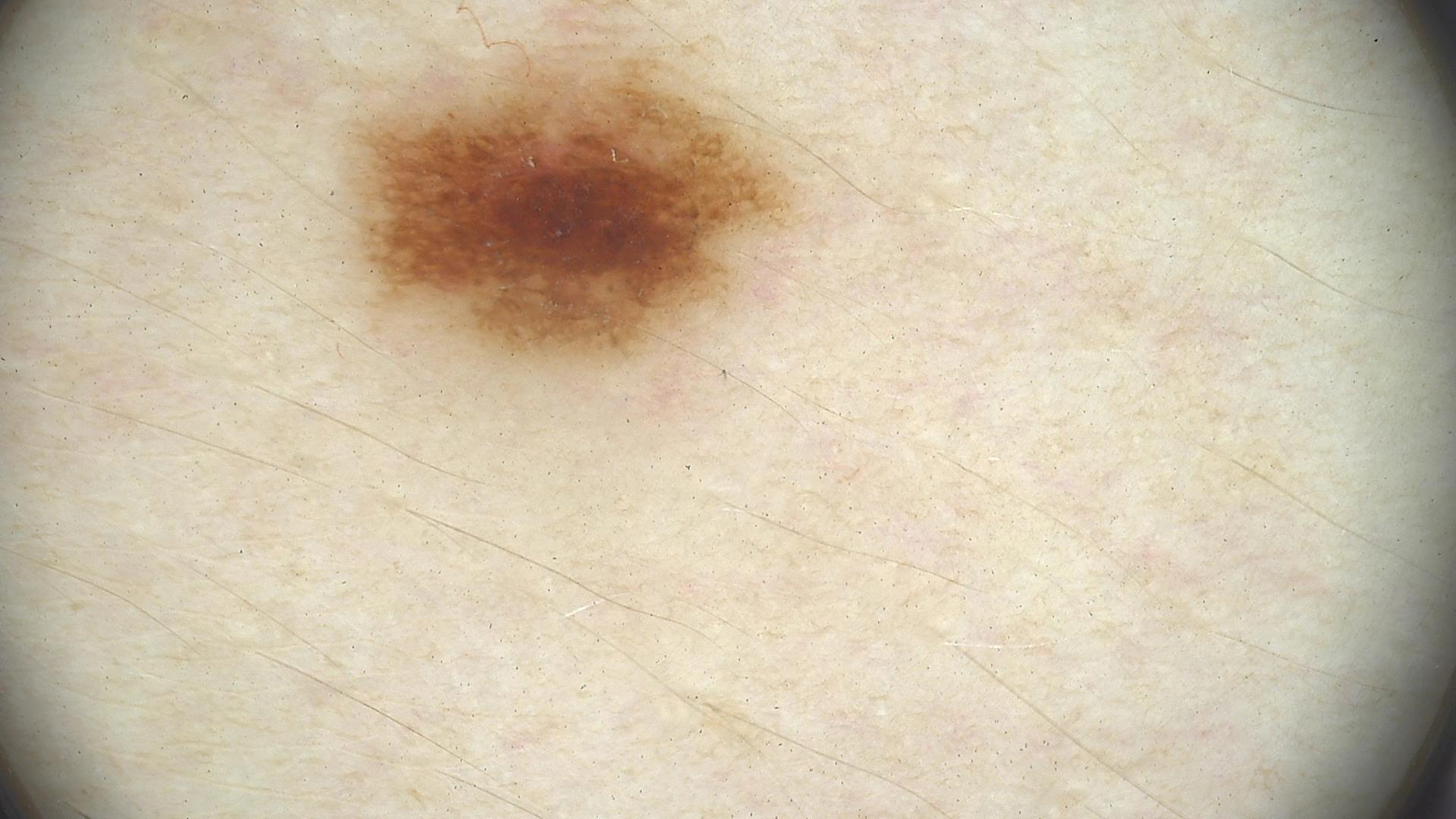Impression:
Consistent with a dysplastic junctional nevus.